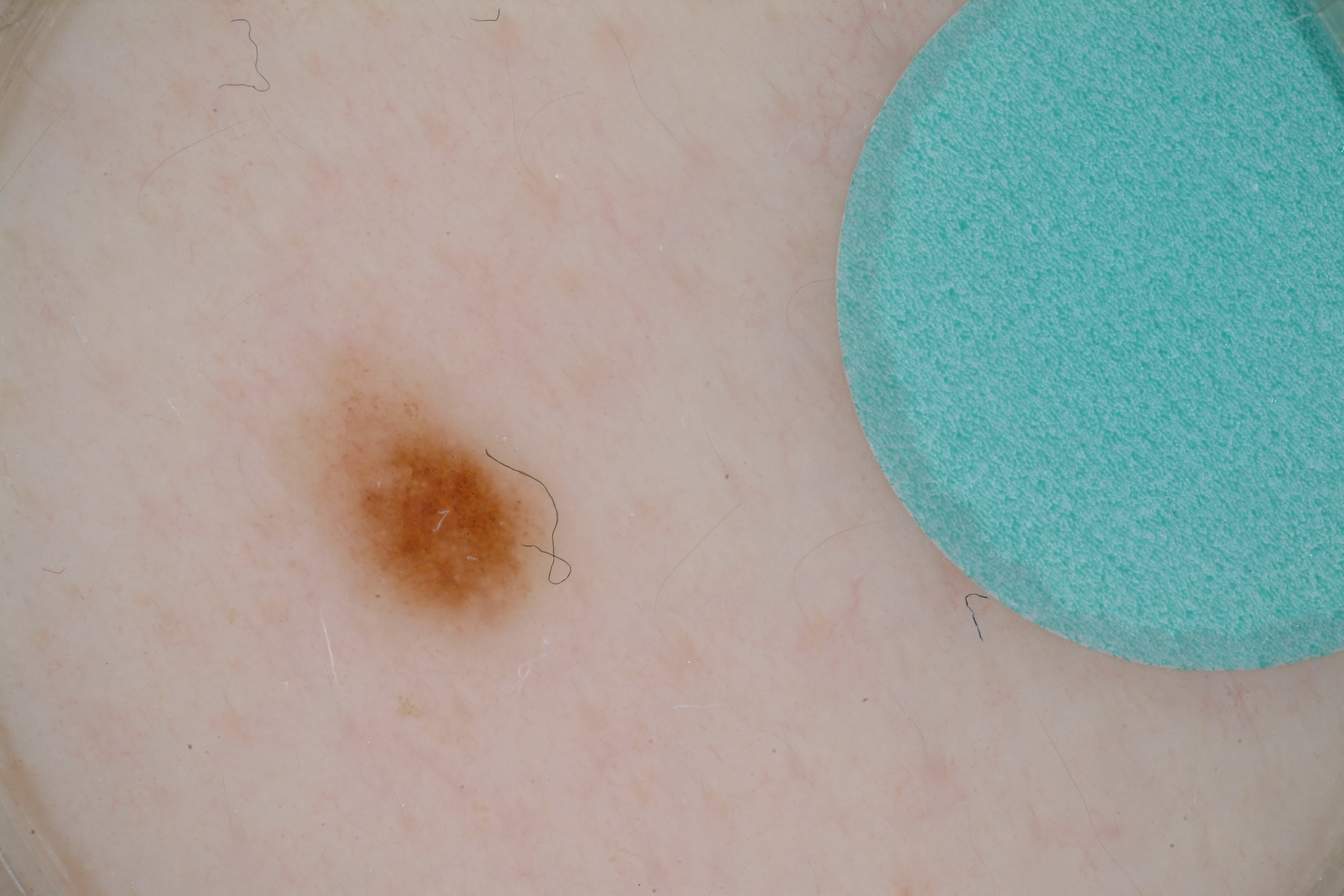Q: What are the patient's age and sex?
A: male, about 15 years old
Q: What kind of image is this?
A: dermoscopy
Q: Lesion extent?
A: small
Q: What dermoscopic features are present?
A: globules; absent: pigment network, milia-like cysts, streaks, and negative network
Q: Where is the lesion in the image?
A: [276,322,594,665]
Q: What is this lesion?
A: a melanocytic nevus, a benign skin lesion